Skin tone: FST VI; human graders estimated 8 on the Monk Skin Tone · the lesion involves the back of the hand, leg and arm · reported lesion symptoms include burning and itching · the photo was captured at a distance:
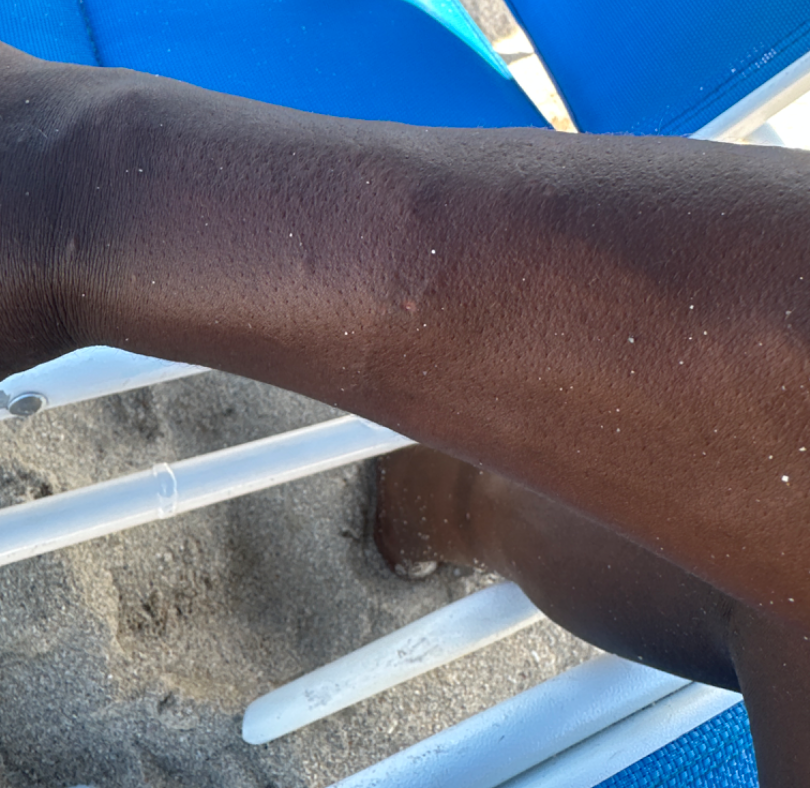Assessment: The condition could not be reliably identified from the image.